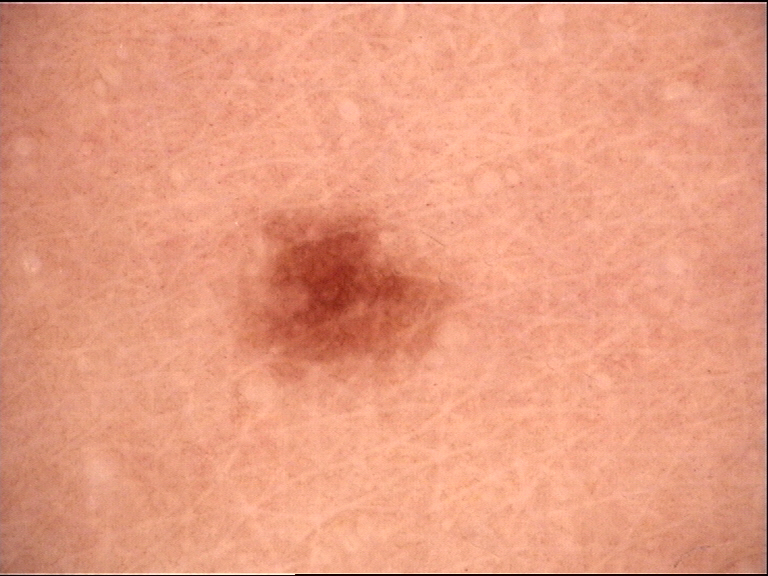The diagnostic label was a junctional nevus.